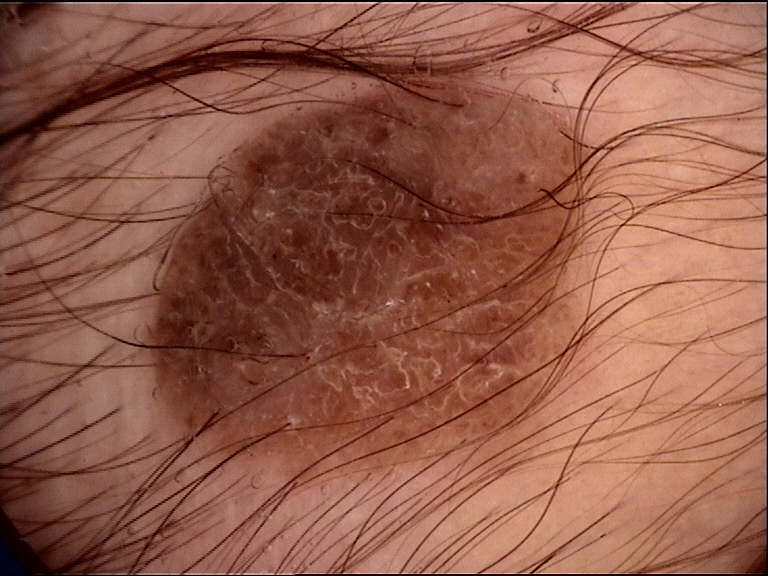Labeled as a banal lesion — a dermal nevus.